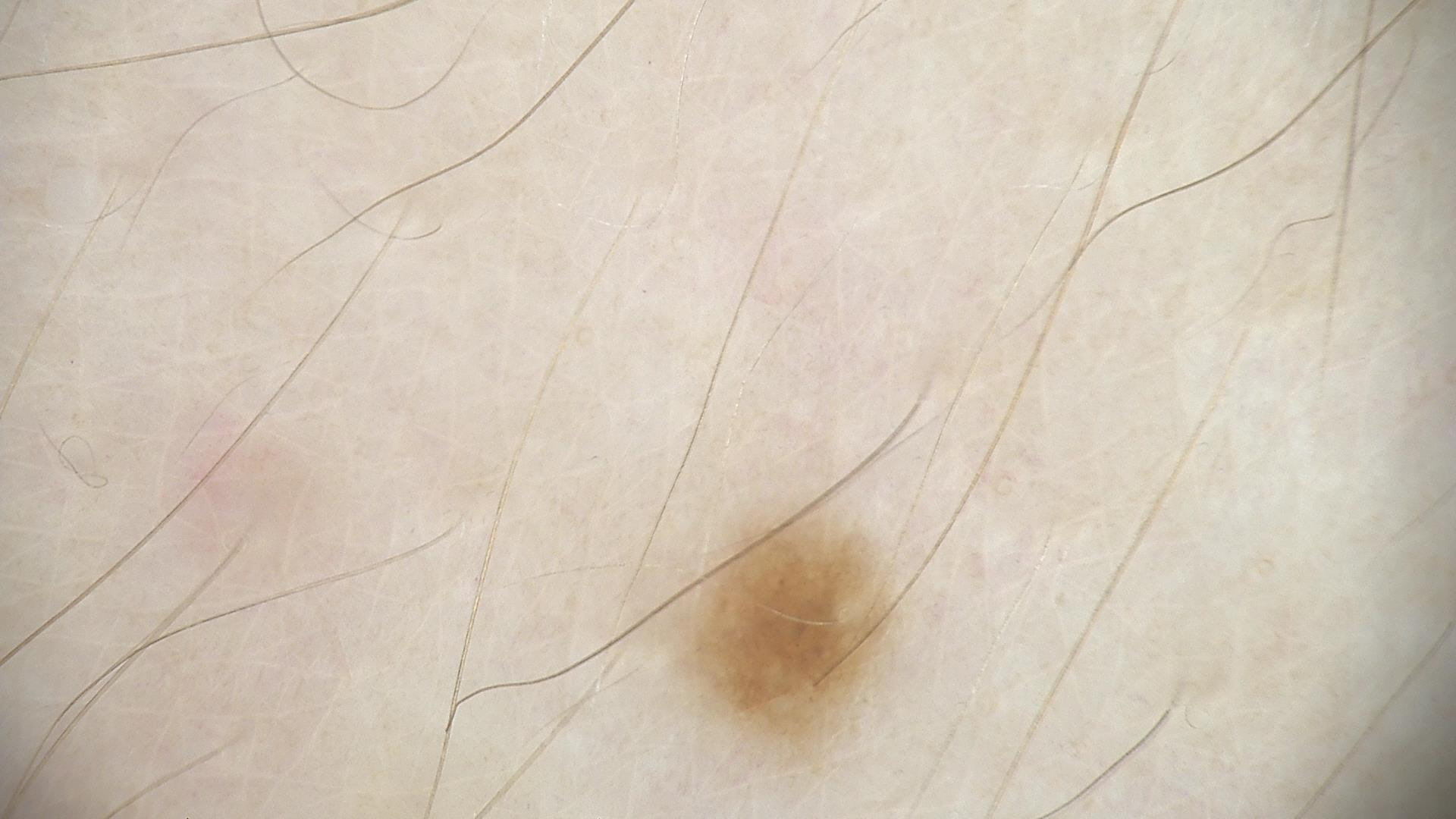The diagnostic label was a dysplastic junctional nevus.